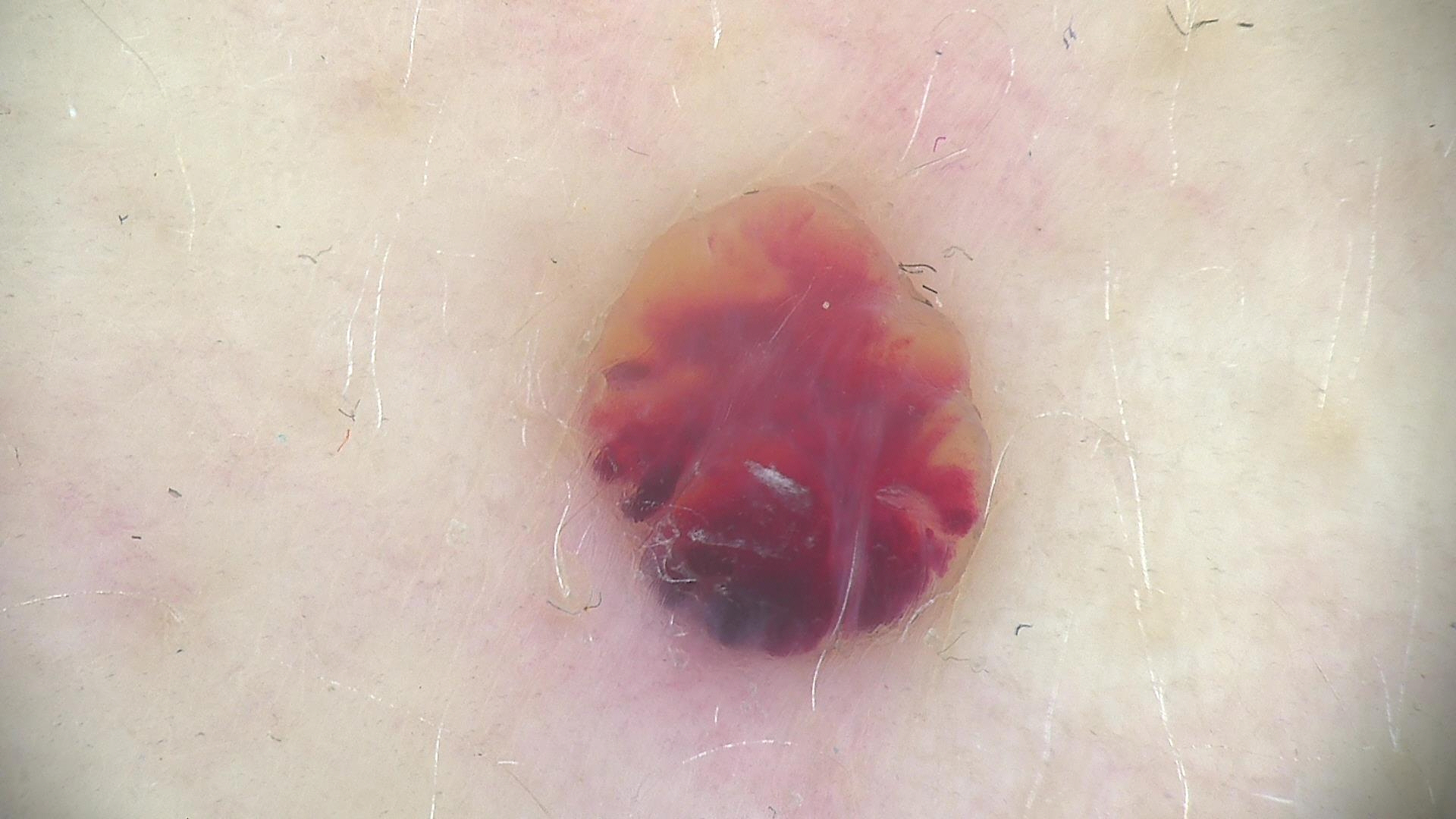A dermoscopy image of a single skin lesion. The diagnosis was a vascular lesion — a lymphangioma.